A skin lesion imaged with a dermatoscope.
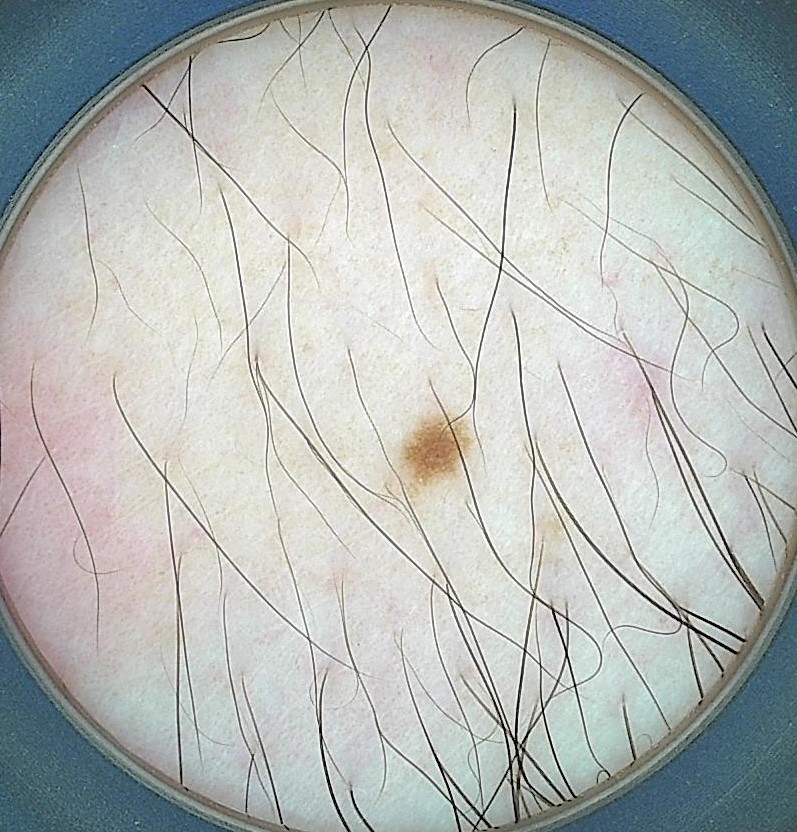Labeled as a banal lesion — a junctional nevus.